A dermoscopic view of a skin lesion: 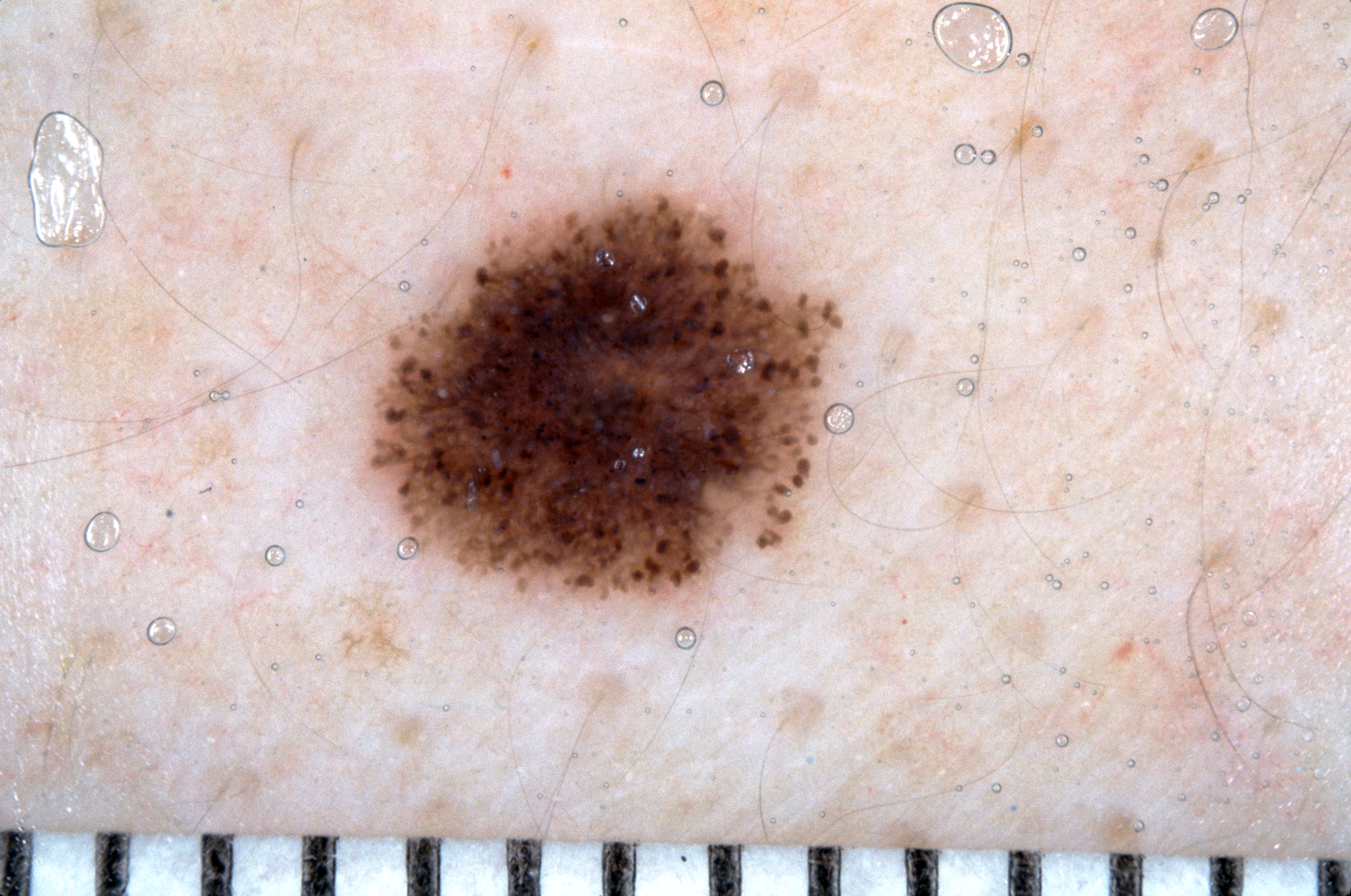Findings: On dermoscopy, the lesion shows streaks and pigment network. As (left, top, right, bottom), the lesion is bounded by <bbox>368, 191, 842, 601</bbox>. Impression: Expert review diagnosed this as a melanocytic nevus, a benign lesion.